Located on the leg; reported duration is less than one week; symptoms reported: bothersome appearance, enlargement and itching; the photo was captured at a distance; the patient considered this skin that appeared healthy to them; the lesion is described as raised or bumpy: 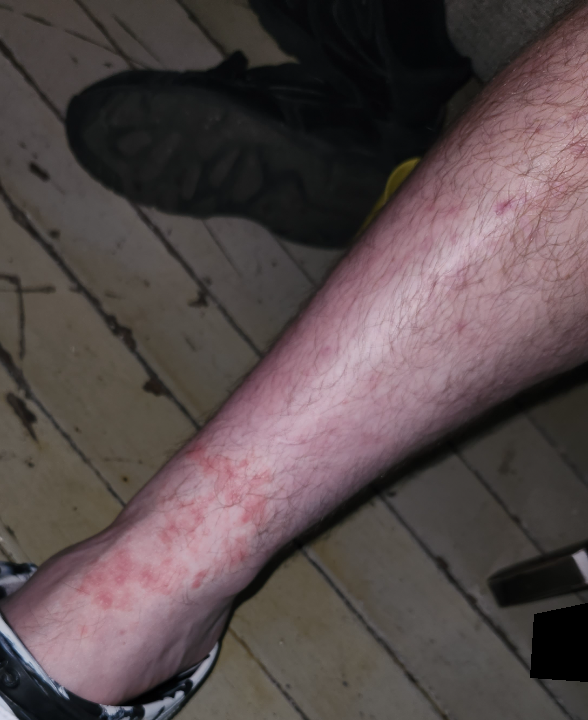The reviewing clinician's impression was: the differential includes Eczema and Allergic Contact Dermatitis, with no clear leading consideration.